A female subject aged approximately 75. Contact-polarized dermoscopy of a skin lesion.
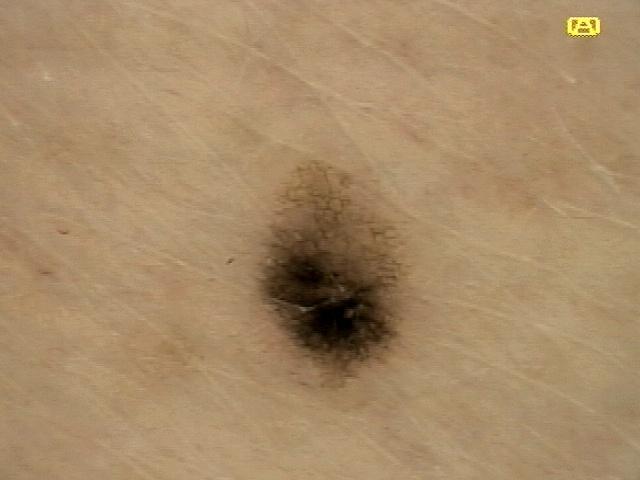site: the trunk; impression: Nevus.